A dermoscopic photograph of a skin lesion.
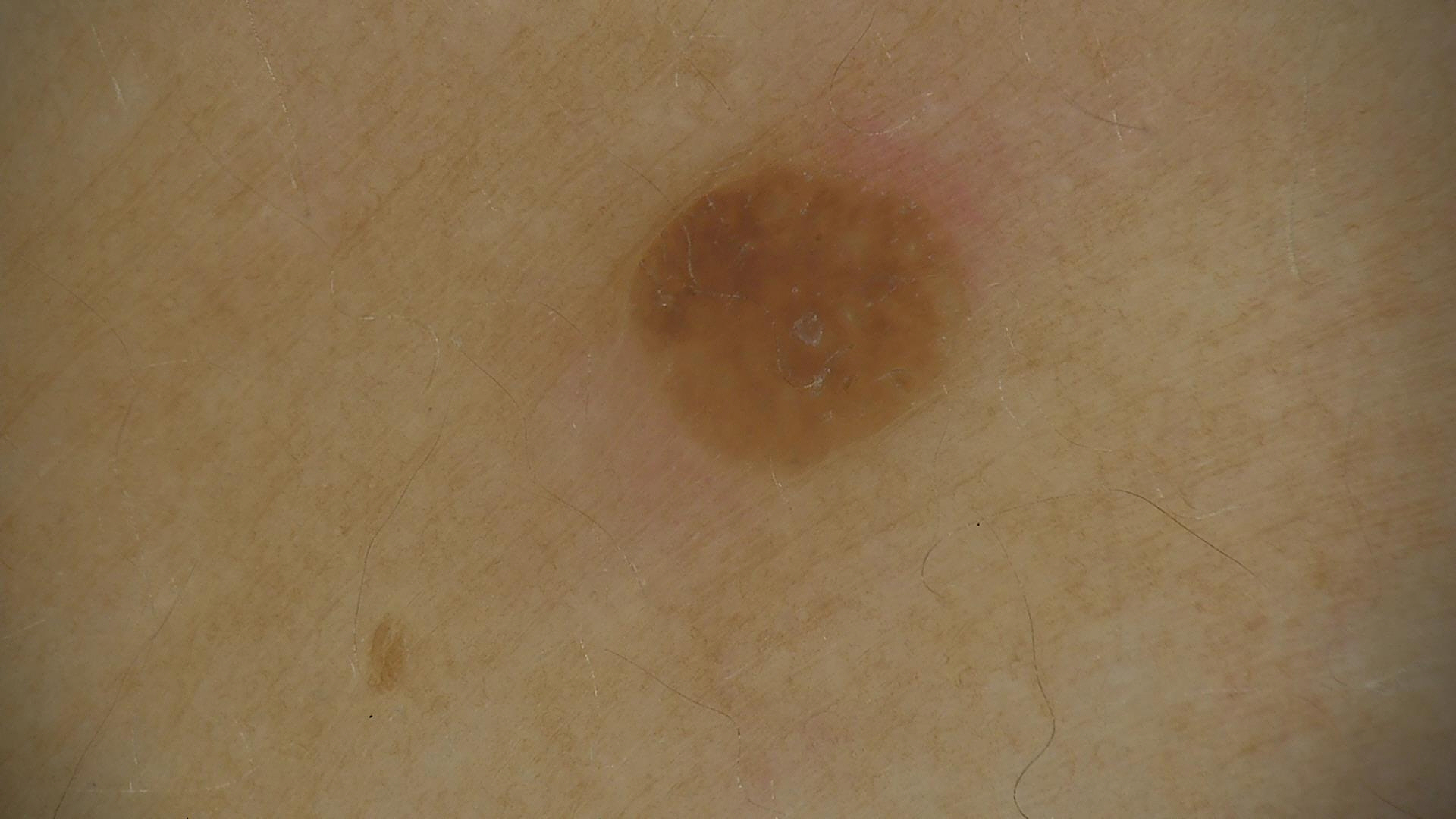Q: How is the lesion classified?
A: keratinocytic
Q: What was the diagnostic impression?
A: seborrheic keratosis (expert consensus)